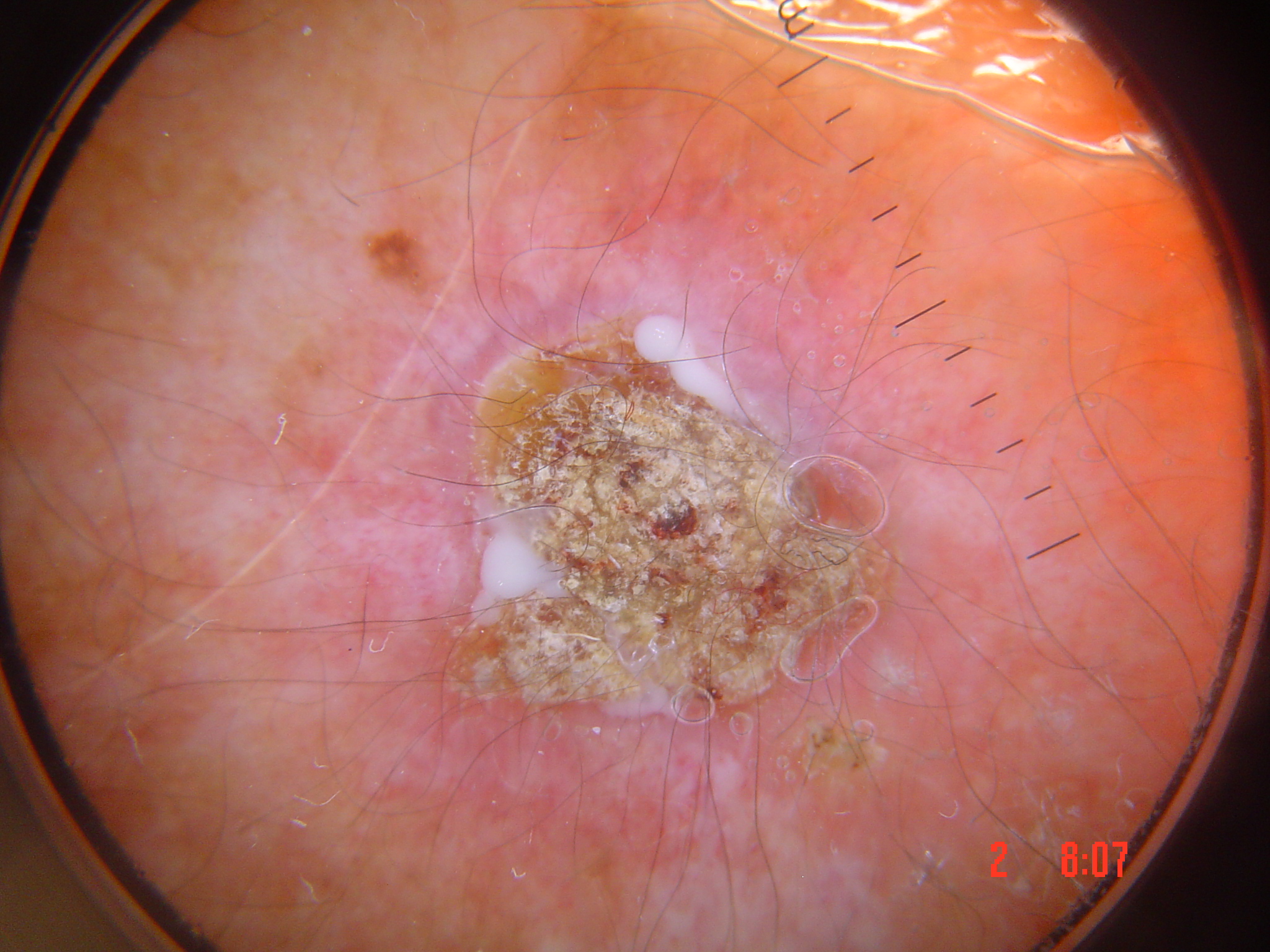Findings: A skin lesion imaged with a dermatoscope. This is a keratinocytic lesion. Diagnosis: Biopsy-confirmed as a malignancy — a squamous cell carcinoma.